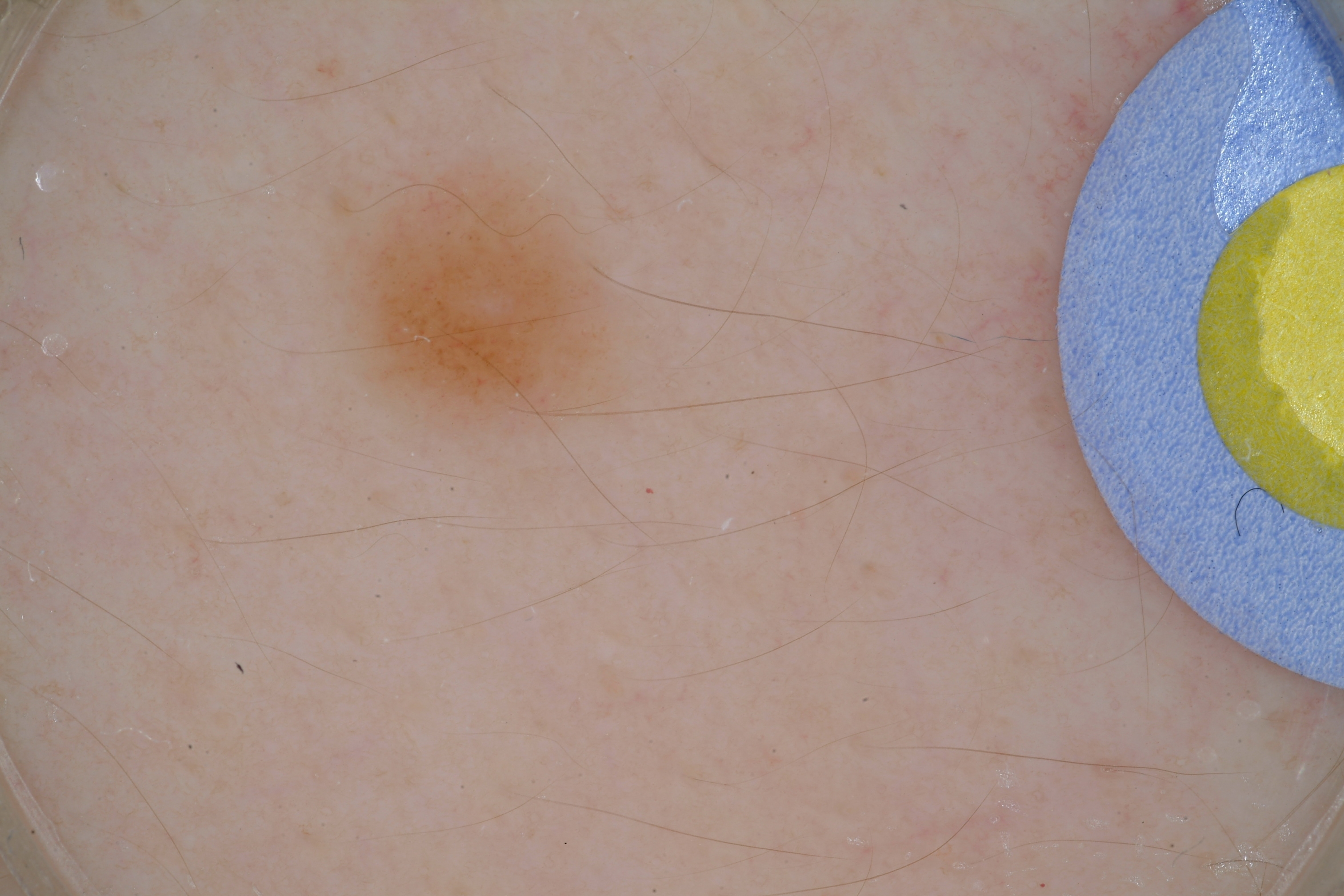<lesion>
<image>
  <modality>dermoscopy</modality>
</image>
<patient>
  <sex>male</sex>
  <age_approx>15</age_approx>
</patient>
<lesion_location>
  <bbox_xyxy>329, 153, 616, 422</bbox_xyxy>
</lesion_location>
<lesion_extent>small</lesion_extent>
<dermoscopic_features>
  <present>milia-like cysts</present>
  <absent>pigment network, globules, streaks, negative network</absent>
</dermoscopic_features>
<diagnosis>
  <name>melanocytic nevus</name>
  <malignancy>benign</malignancy>
  <lineage>melanocytic</lineage>
  <provenance>clinical</provenance>
</diagnosis>
</lesion>